The photo was captured at a distance; the affected area is the arm, leg and front of the torso; male subject, age 40–49.
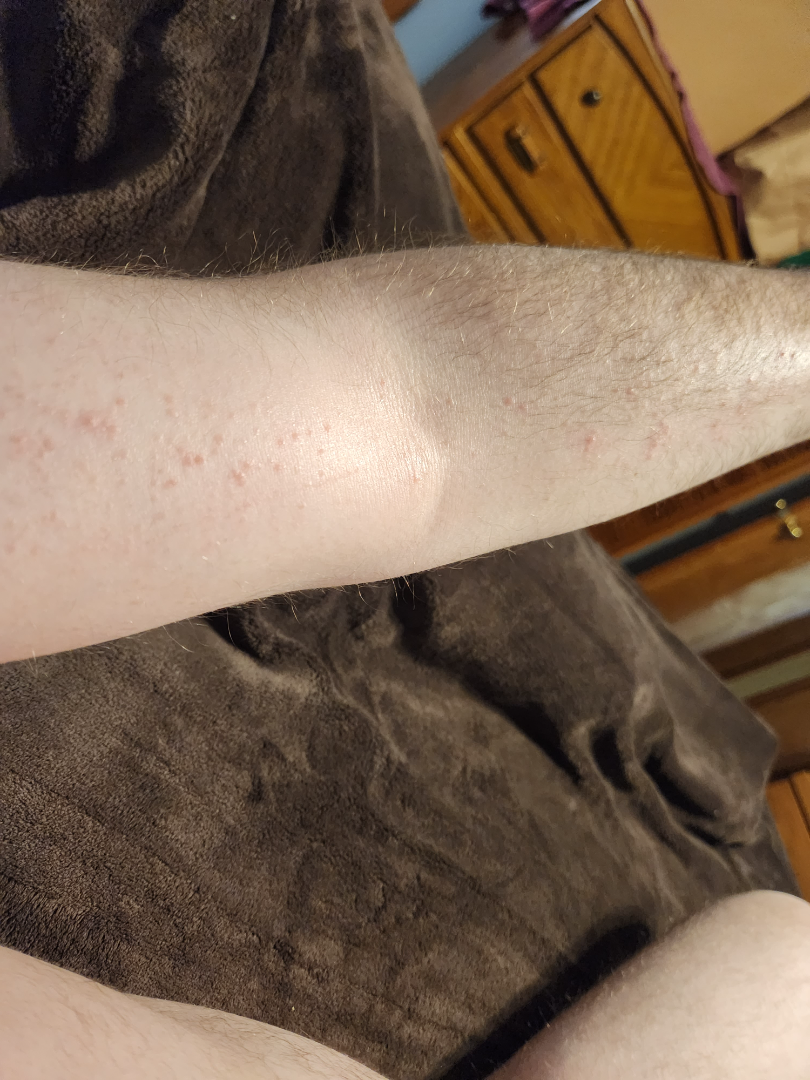Self-categorized by the patient as a rash. Reported duration is less than one week. The lesion is described as raised or bumpy. Symptoms reported: itching. The favored diagnosis is Eczema; possibly Irritant Contact Dermatitis; also raised was Allergic Contact Dermatitis; a remote consideration is Folliculitis.